A female subject aged approximately 75. A dermoscopic close-up of a skin lesion — 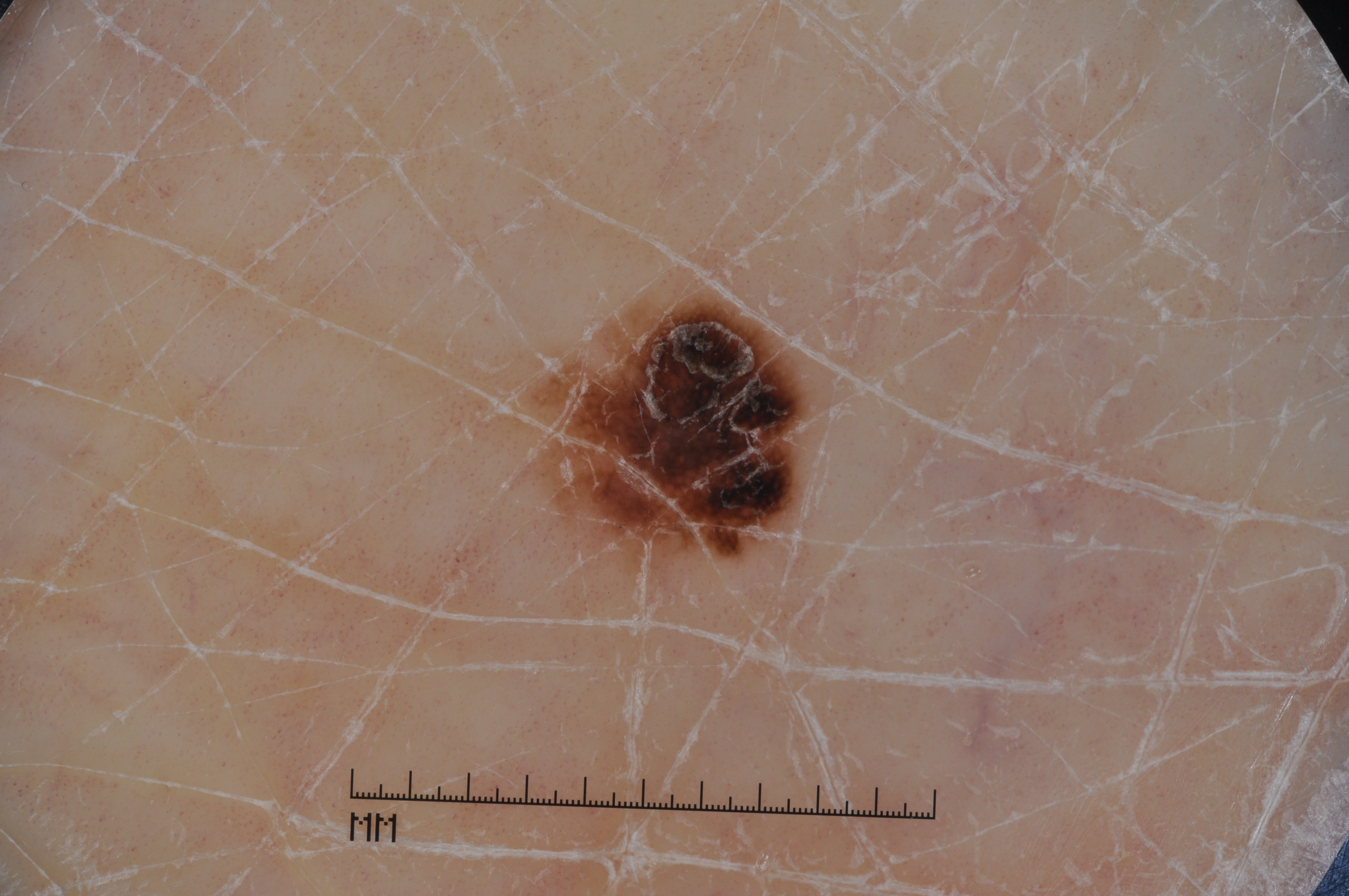Dermoscopic assessment notes pigment network.
A small lesion within a wider field of skin.
In (x1, y1, x2, y2) order, the lesion occupies the region (548, 301, 811, 560).
Histopathology confirmed a melanoma, a malignant lesion.